The photo was captured at an angle · reported lesion symptoms include itching and burning · the patient considered this a rash · the patient also reports fatigue and fever · female subject, age 50–59 · located on the back of the torso · the contributor notes the condition has been present for less than one week — 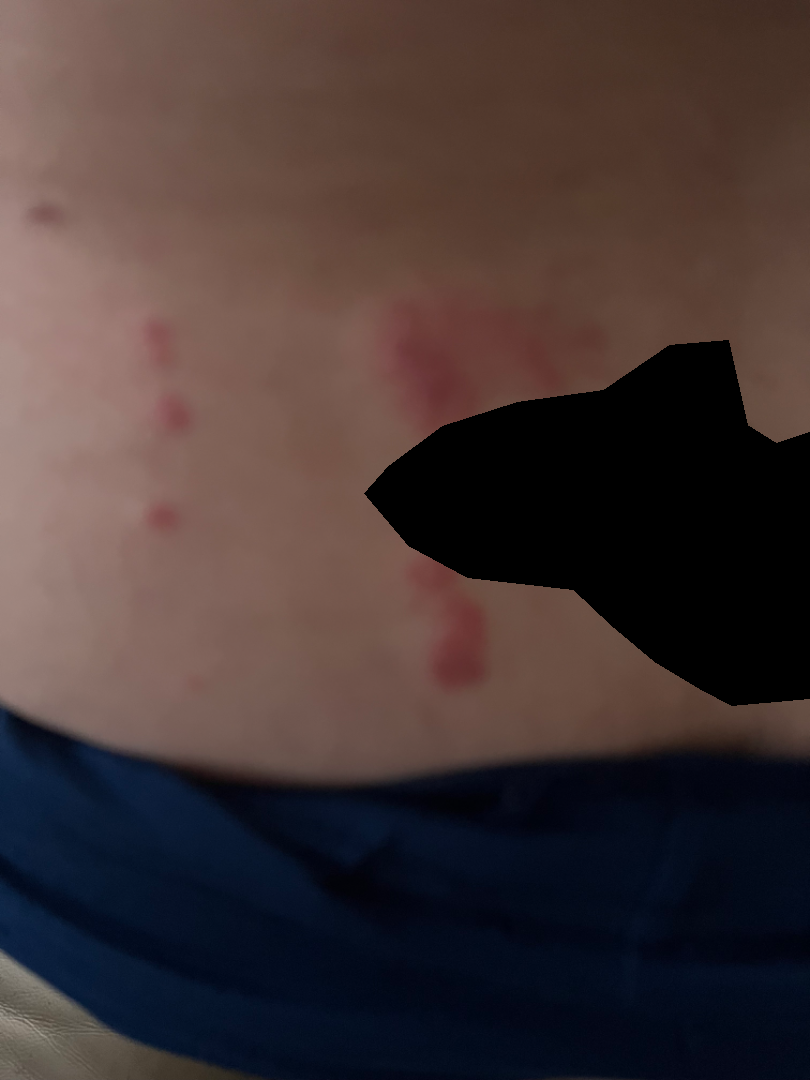On remote dermatologist review, the leading consideration is Allergic Contact Dermatitis; possibly Herpes Zoster.